The patient is a female aged 30–39; the photograph is a close-up of the affected area; the lesion involves the arm:
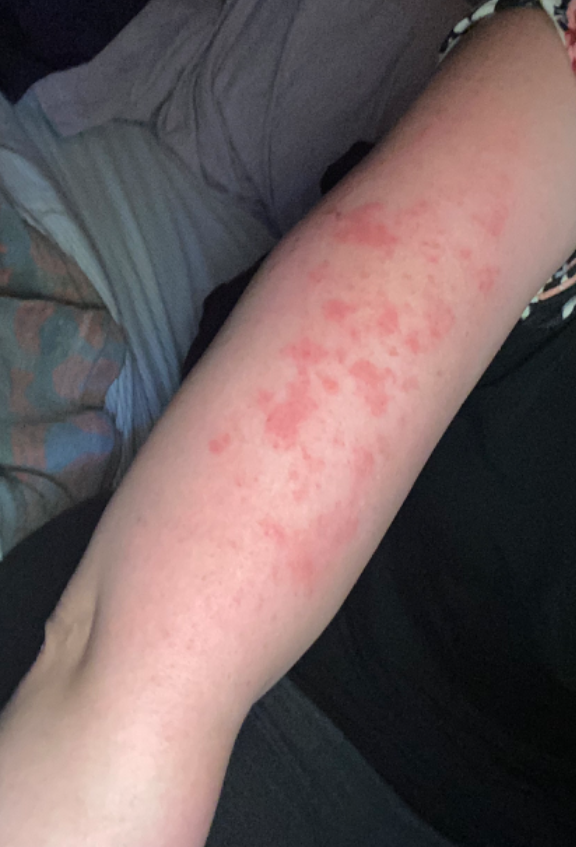assessment: could not be assessed | patient describes the issue as: a rash | described texture: raised or bumpy | present for: one to four weeks.